History notes prior skin cancer (patient or family), no pesticide exposure, and no alcohol use:
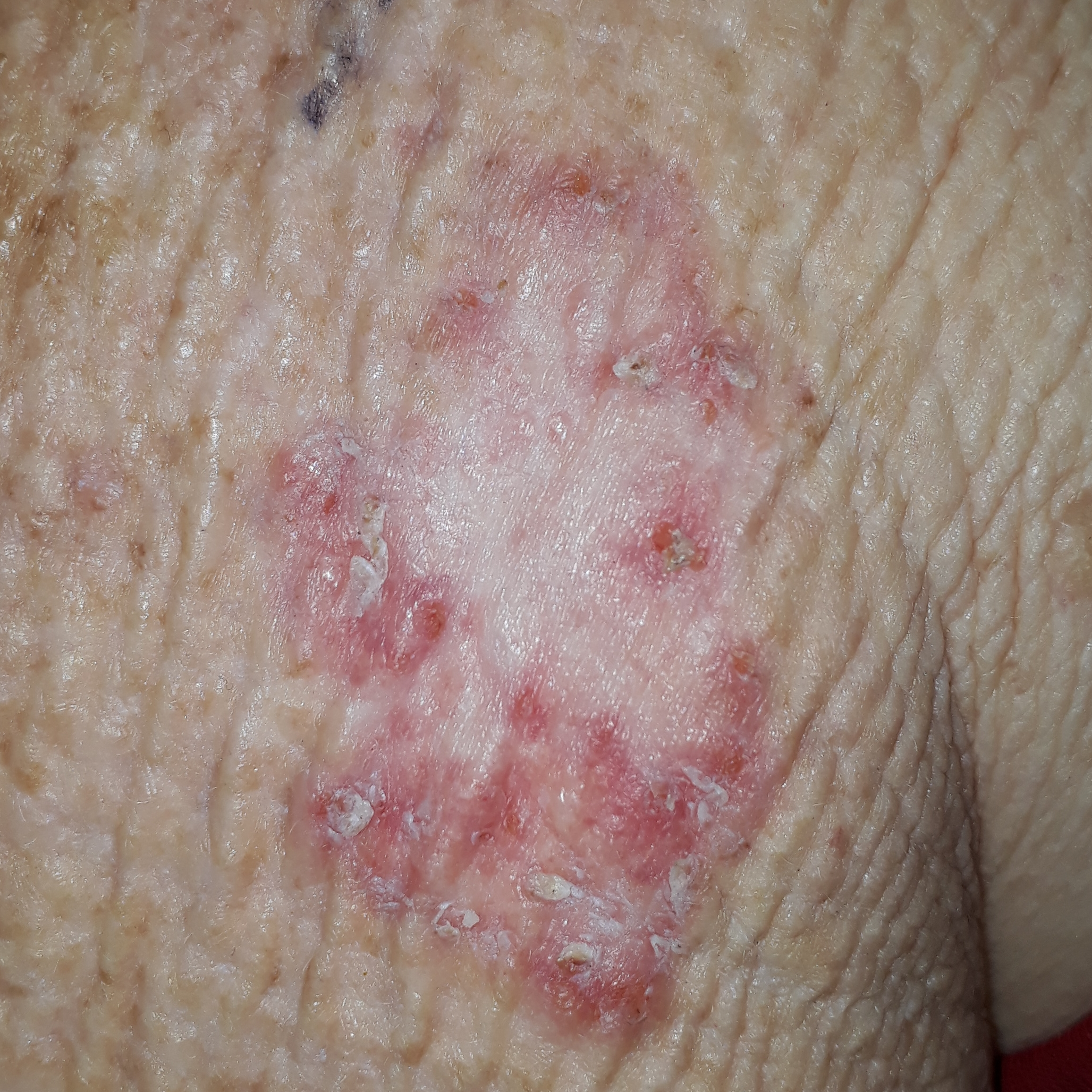The lesion is on the chest.
Histopathologically confirmed as a basal cell carcinoma.